A moderate number of moles by the patient's own estimate · referred with a clinical suspicion of seborrheic keratosis · the patient says their skin tans without first burning · on a questionnaire the patient reported a personal history of cancer, a family history of skin cancer, and no personal history of skin cancer · a dermoscopy image of a skin lesion:
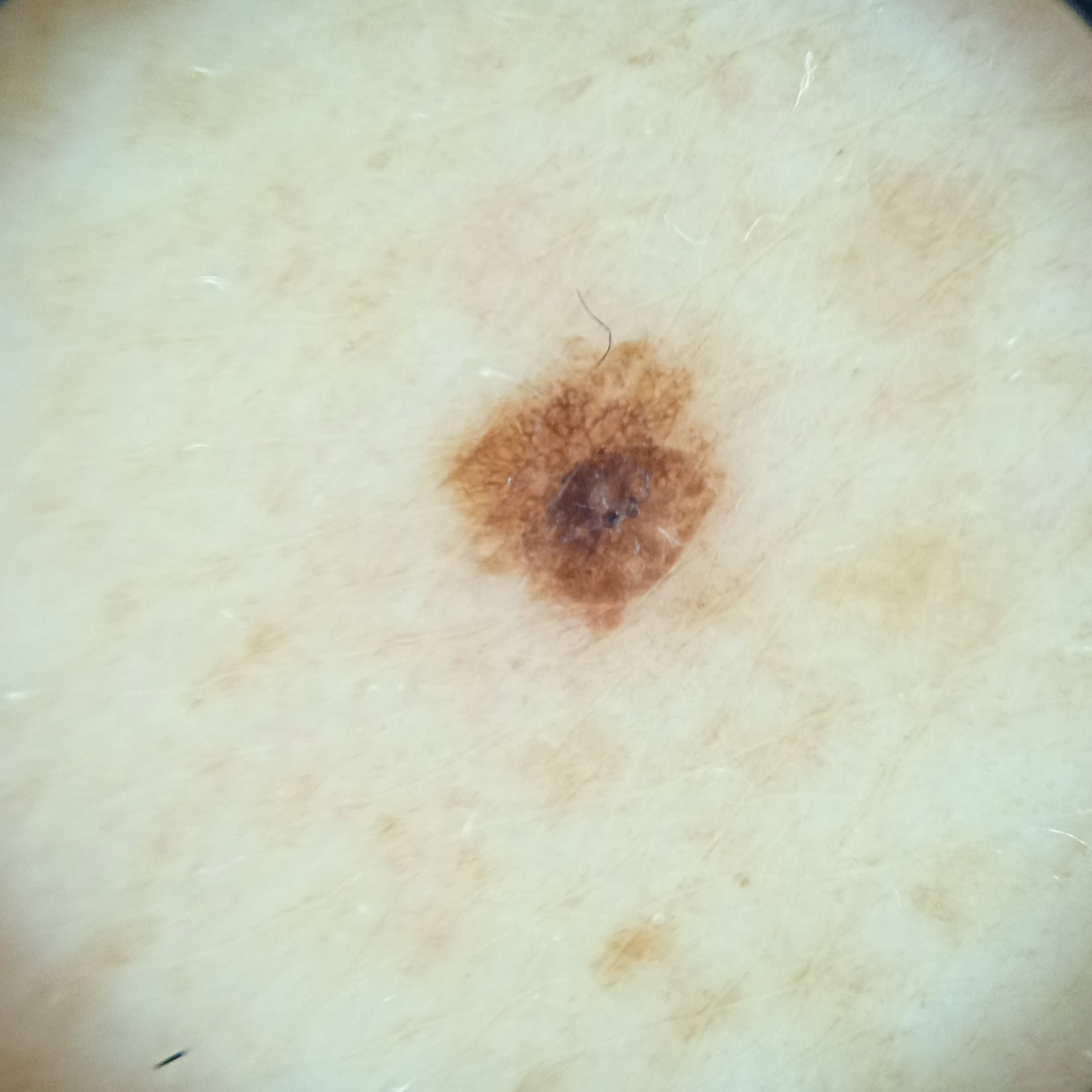{"diagnosis": {"name": "seborrheic keratosis", "malignancy": "benign", "procedure": "excision"}}